A skin lesion imaged with a dermatoscope.
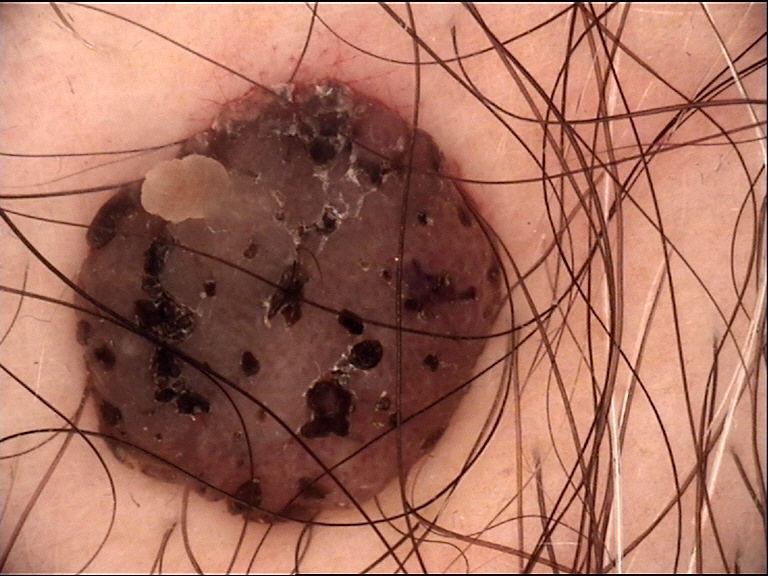| feature | finding |
|---|---|
| classification | banal |
| assessment | dermal nevus (expert consensus) |